On a questionnaire the patient reported a family history of skin cancer, a personal history of skin cancer, and immunosuppression. The patient says their skin reddens painfully with sun exposure. Collected as part of a research study, without a referral diagnosis. The patient describes having numerous moles. A male subject aged 65. A dermoscopy image of a skin lesion.
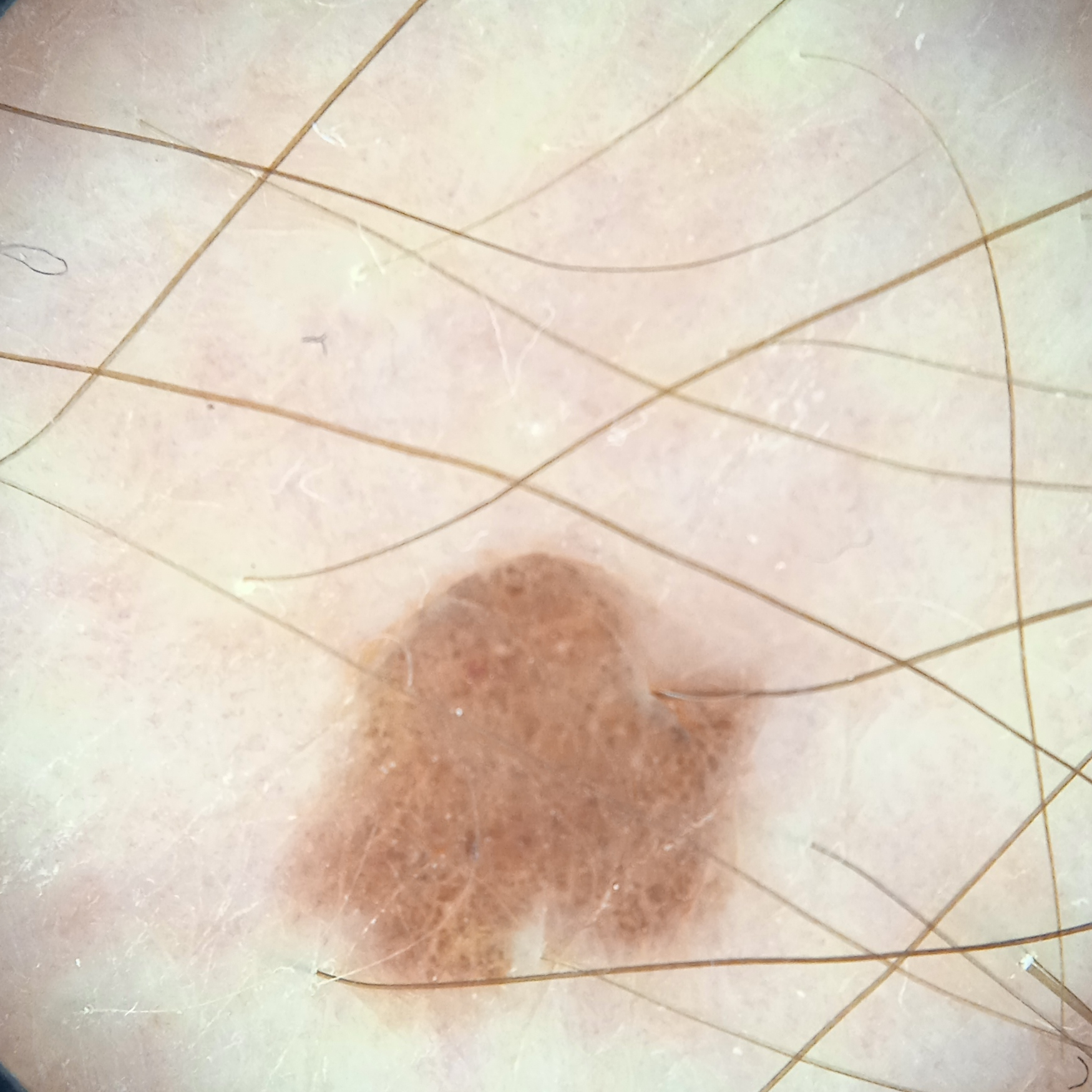  lesion_location: an arm
  diagnosis:
    name: melanocytic nevus
    malignancy: benign